Reported duration is less than one week · the patient described the issue as skin that appeared healthy to them · the affected area is the arm · the photograph was taken at a distance · Fitzpatrick skin type III; lay reviewers estimated Monk skin tone scale 2 or 3 (two reviewer pools) · the patient did not report lesion symptoms · texture is reported as raised or bumpy:
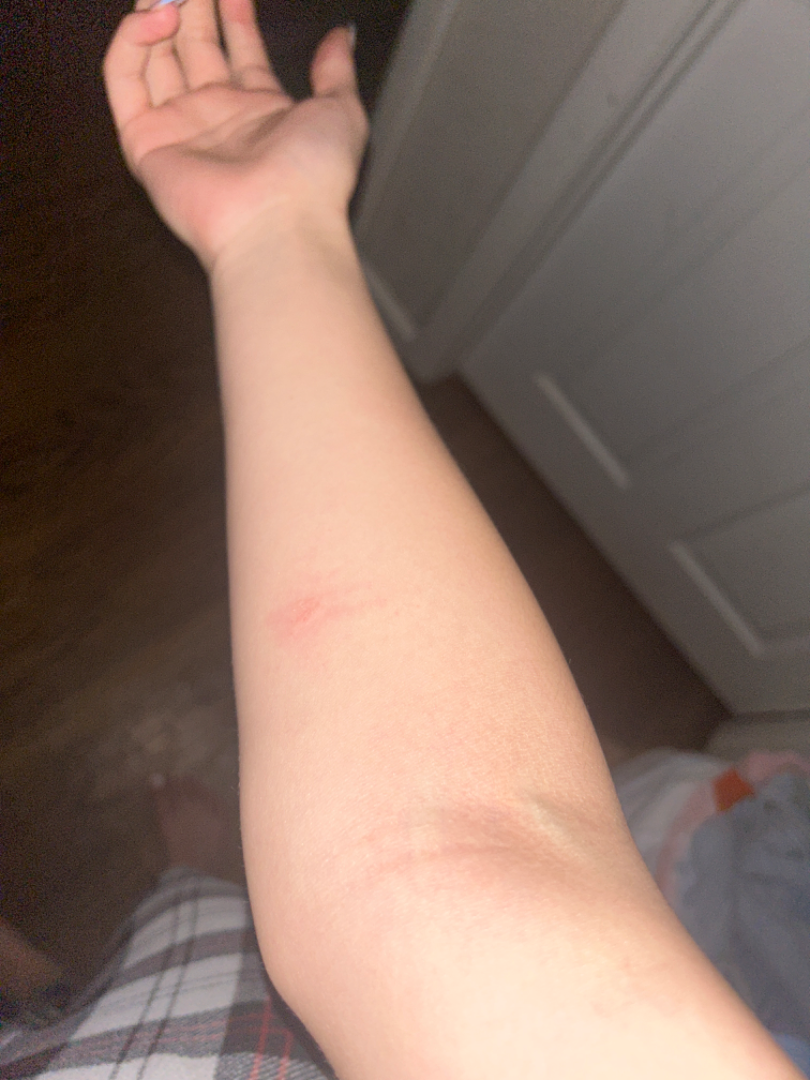| feature | finding |
|---|---|
| assessment | unable to determine |